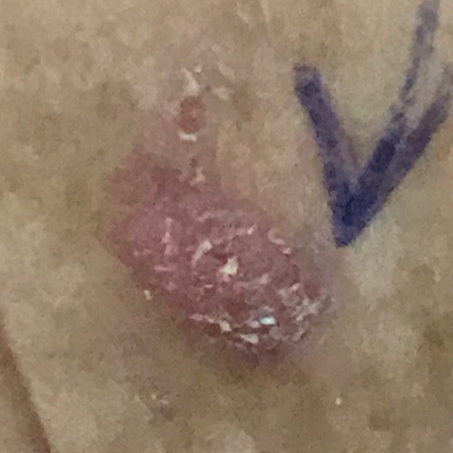{
  "lesion_location": "the face",
  "symptoms": {
    "present": [
      "itching",
      "growth",
      "bleeding",
      "elevation"
    ]
  },
  "diagnosis": {
    "name": "actinic keratosis",
    "code": "ACK",
    "malignancy": "indeterminate",
    "confirmation": "clinical consensus"
  }
}